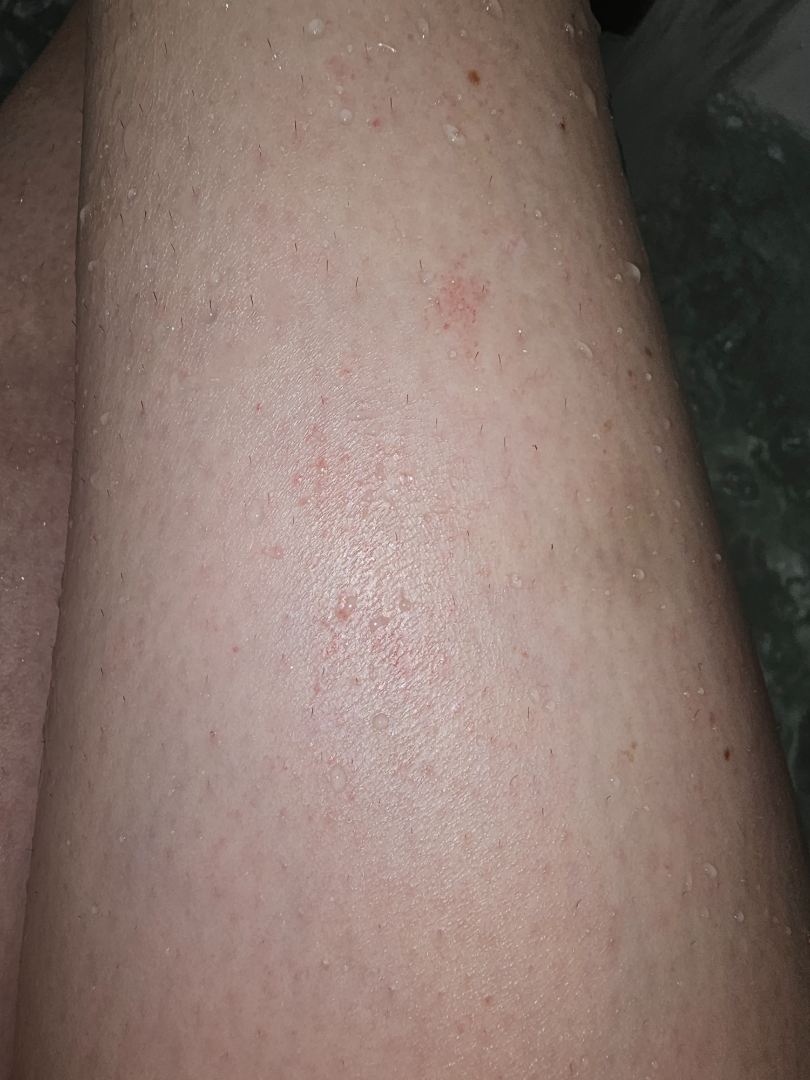Impression:
The image was not sufficient for the reviewer to characterize the skin condition.
History:
The condition has been present for one to four weeks. The lesion involves the arm and leg. The photograph is a close-up of the affected area. The lesion is associated with itching.